The photograph is a close-up of the affected area. The contributor notes the lesion is raised or bumpy. The contributor notes bothersome appearance and itching. The lesion involves the arm. Self-categorized by the patient as skin that appeared healthy to them — 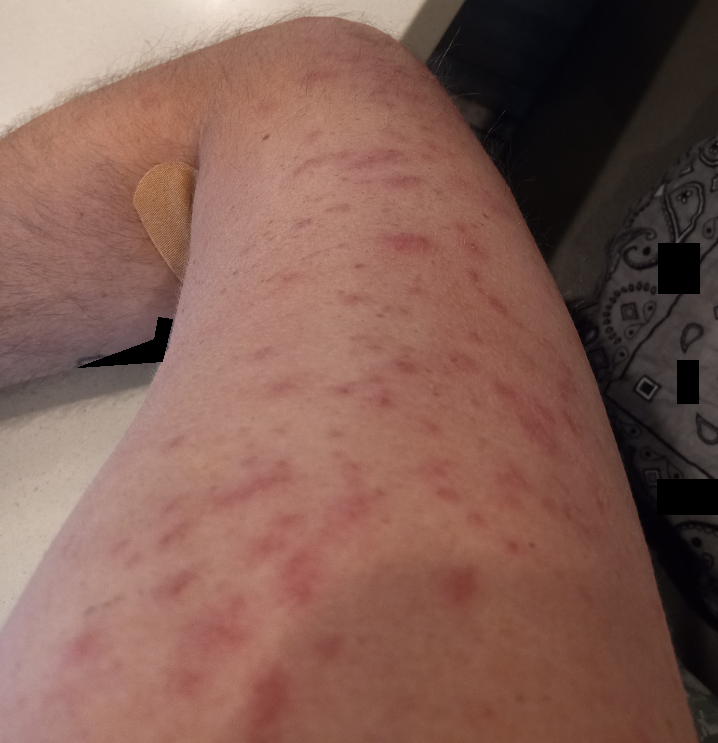Acne and Folliculitis were each considered, in no particular order.